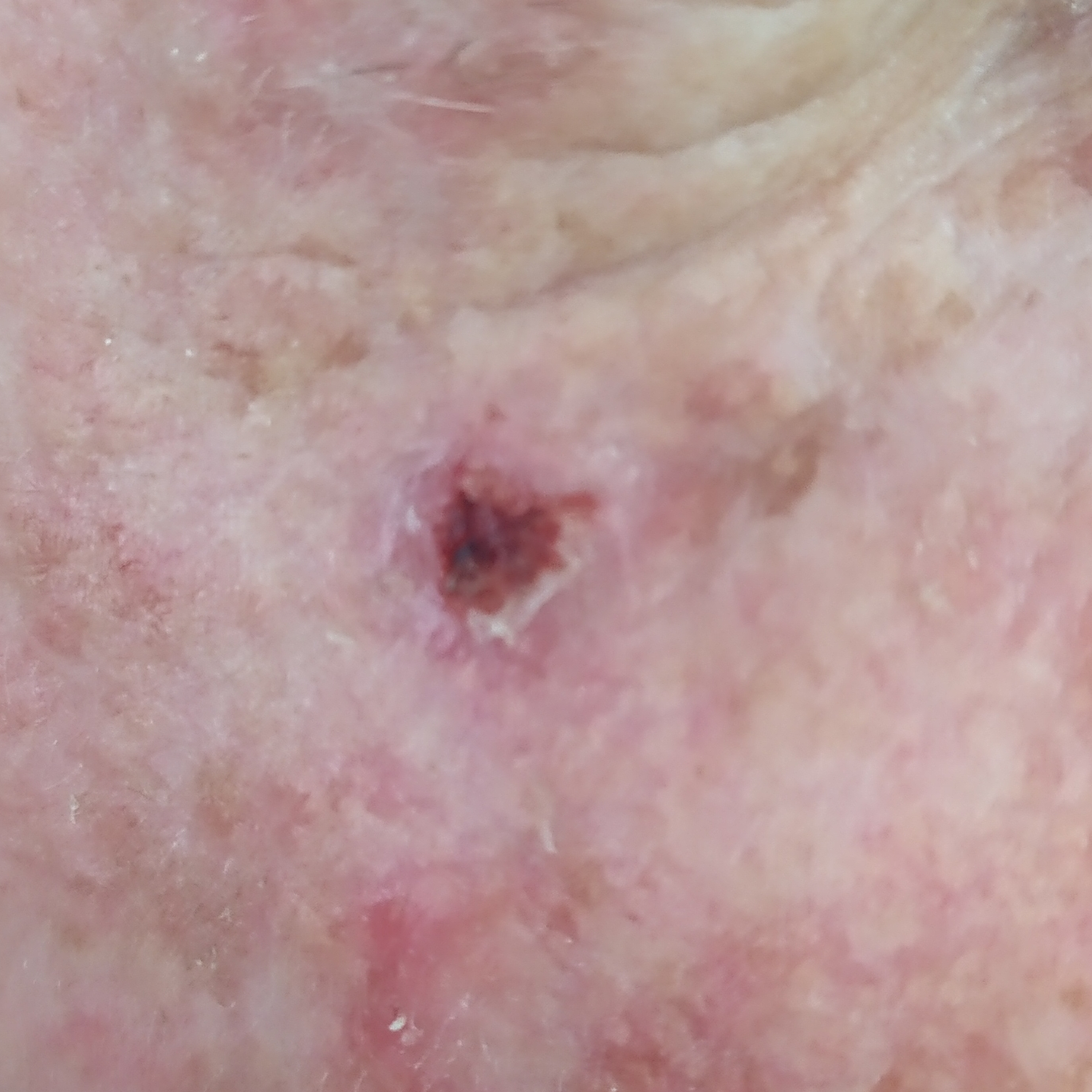Findings:
* exposure history — pesticide exposure, prior skin cancer (patient or family), alcohol use, prior malignancy (patient or family), no tobacco use
* modality — clinical photograph
* skin phototype — IV
* site — the face
* diameter — approx. 7 × 6 mm
* symptoms — itching, elevation, bleeding / no growth, no pain
* pathology — basal cell carcinoma (biopsy-proven)